Skin tone: Fitzpatrick I; lay reviewers estimated Monk skin tone scale 3 or 4. Close-up view: 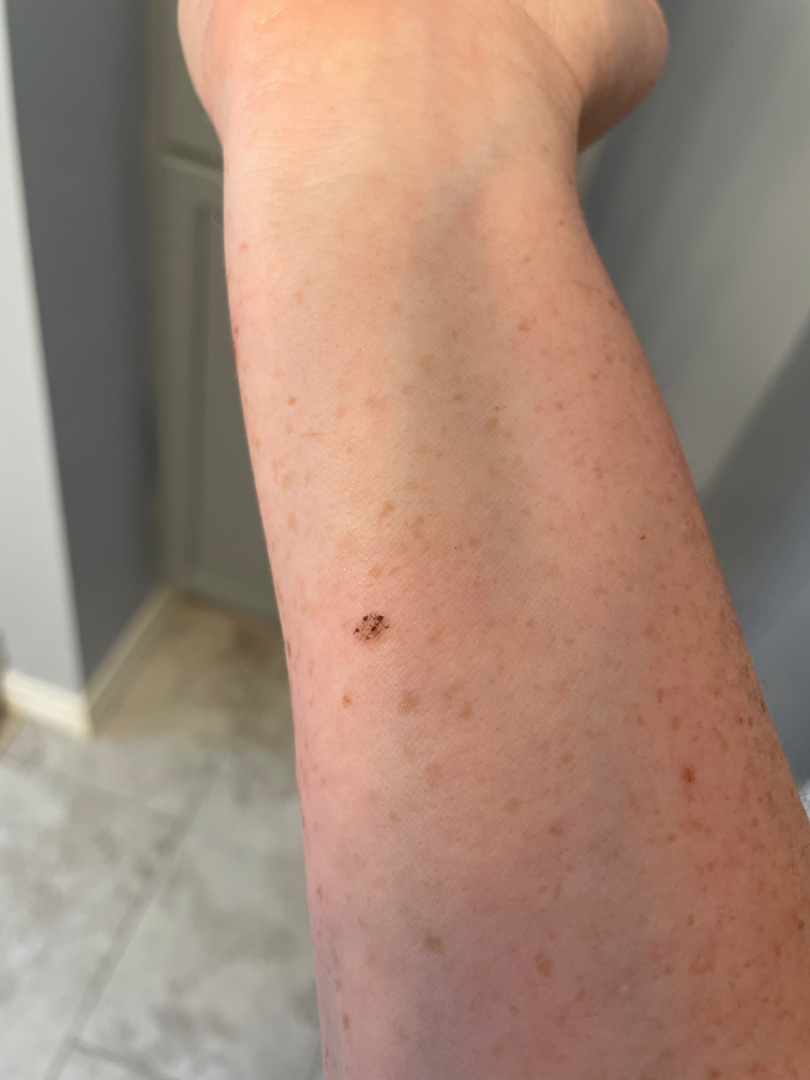<summary>
<differential>
  <SK/ISK>0.55</SK/ISK>
  <Melanocytic Nevus>0.27</Melanocytic Nevus>
  <Atypical Nevus>0.18</Atypical Nevus>
</differential>
</summary>